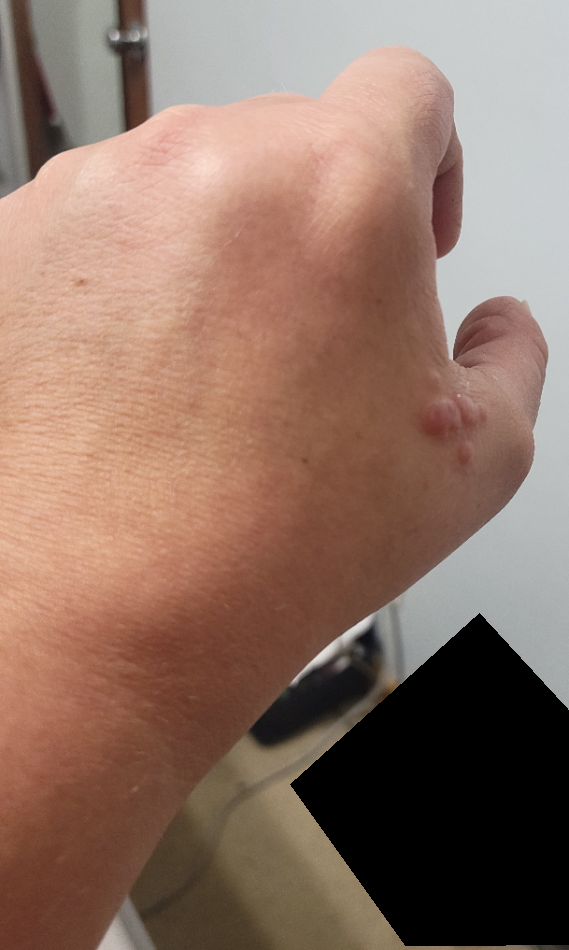assessment=indeterminate from the photograph | framing=at an angle | patient=female, age 40–49 | affected area=back of the hand.